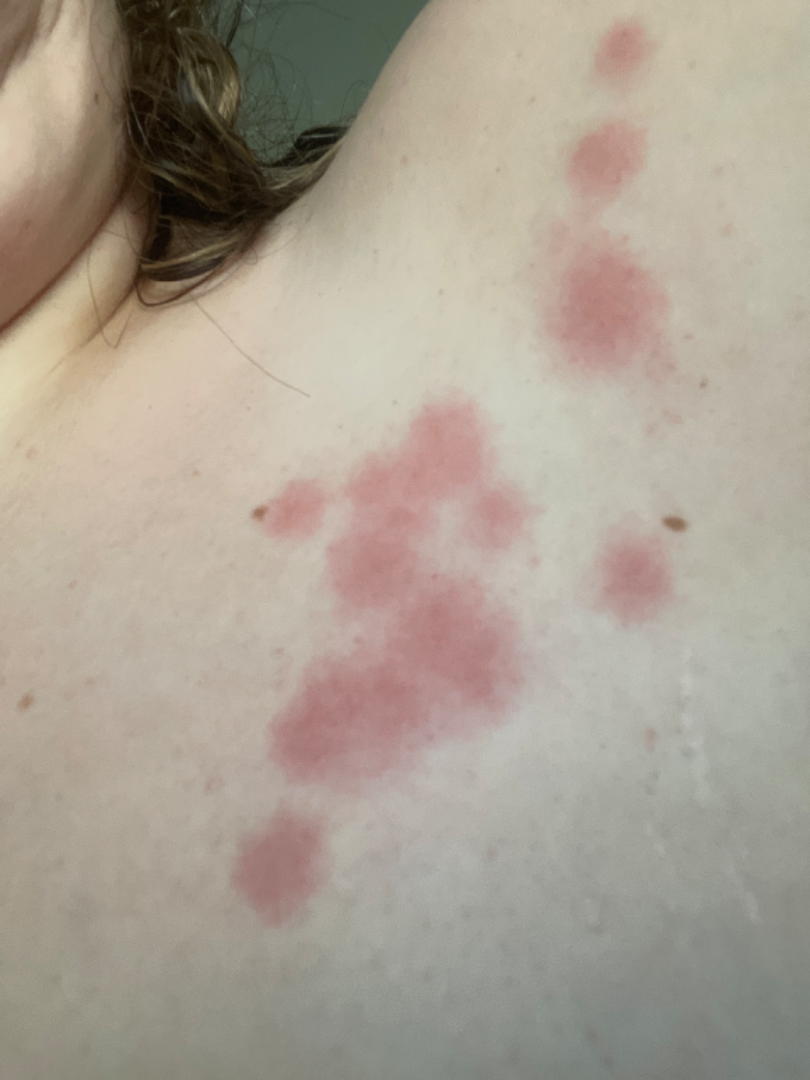Findings:
On remote review of the image, favoring Insect Bite; an alternative is Urticaria; also consider Allergic Contact Dermatitis.